A female subject in their mid-50s:
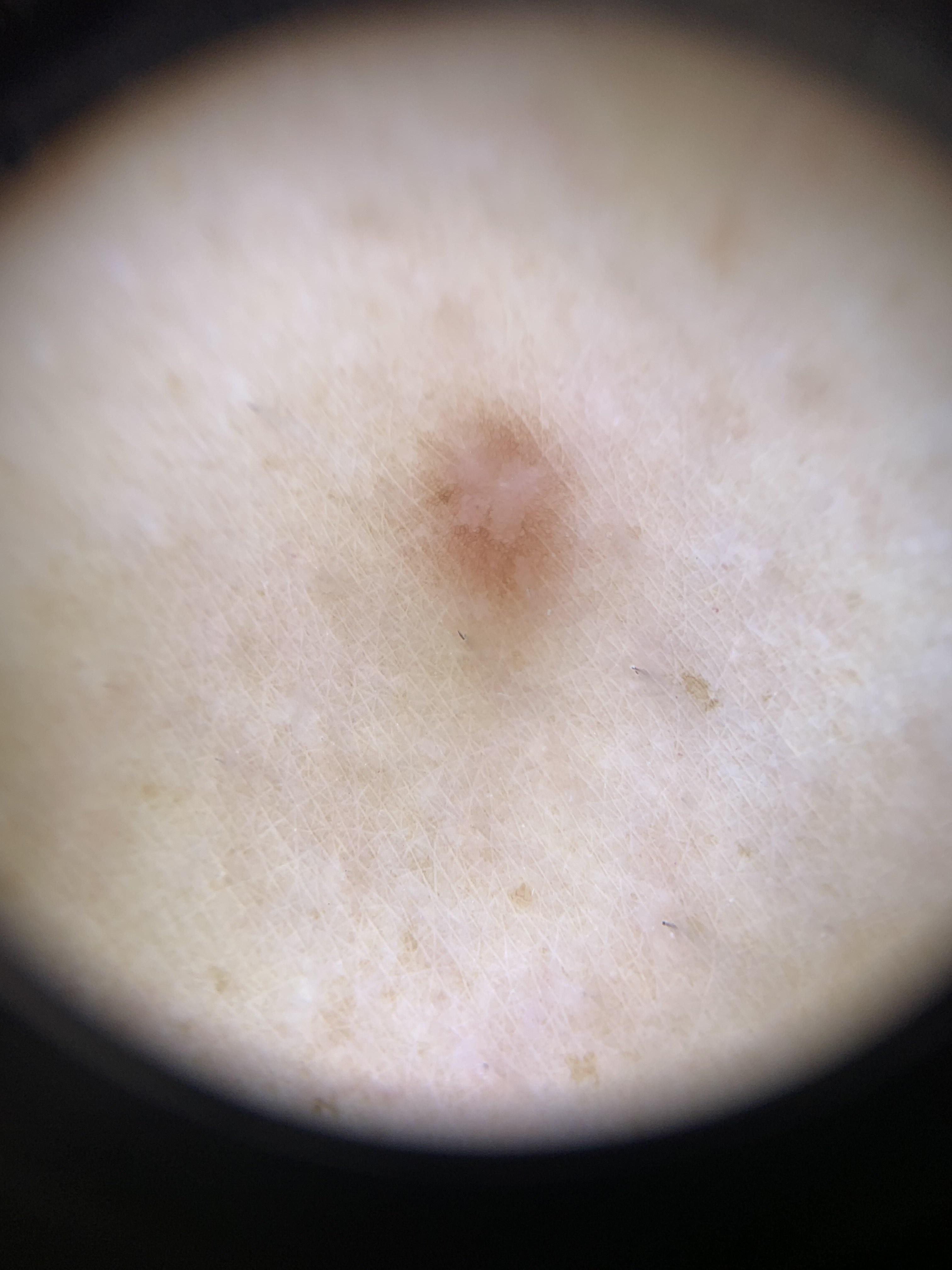{"diagnosis": {"name": "Dermatofibroma", "malignancy": "benign", "confirmation": "expert clinical impression", "lineage": "fibro-histiocytic"}}